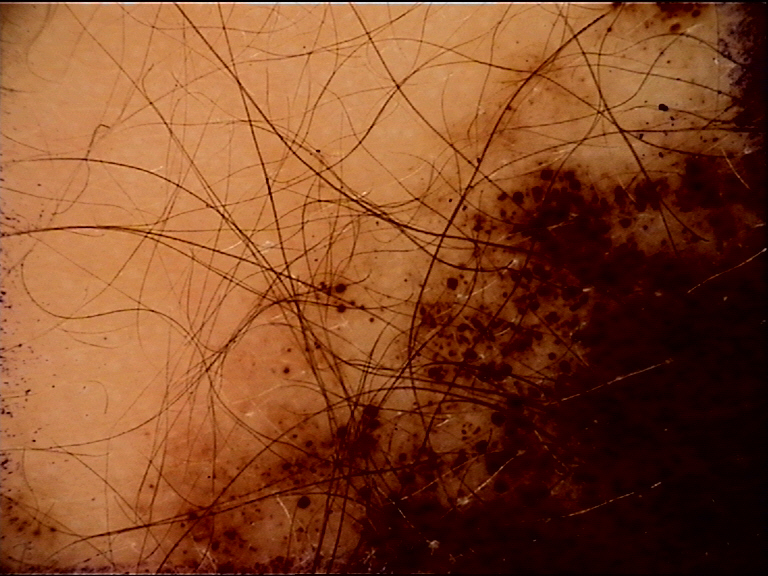Dermoscopy of a skin lesion.
The architecture is that of a banal lesion.
Classified as a congenital compound nevus.